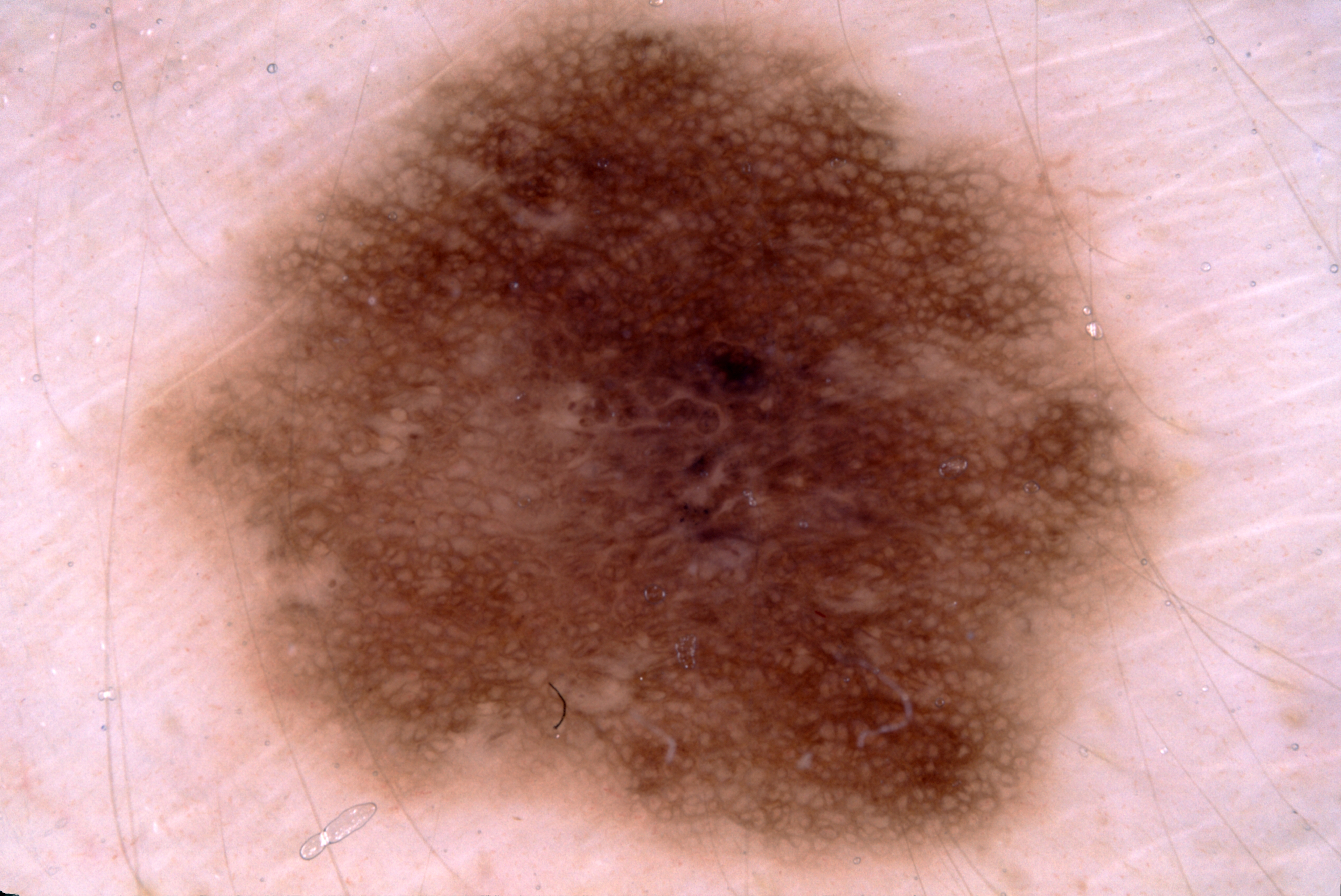A female patient roughly 30 years of age. A dermoscopic close-up of a skin lesion. In (x1, y1, x2, y2) order, the lesion spans <box>136, 14, 1184, 875</box>. The lesion covers approximately 55% of the dermoscopic field. Dermoscopically, the lesion shows pigment network and negative network. The diagnostic assessment was a melanocytic nevus, a benign skin lesion.